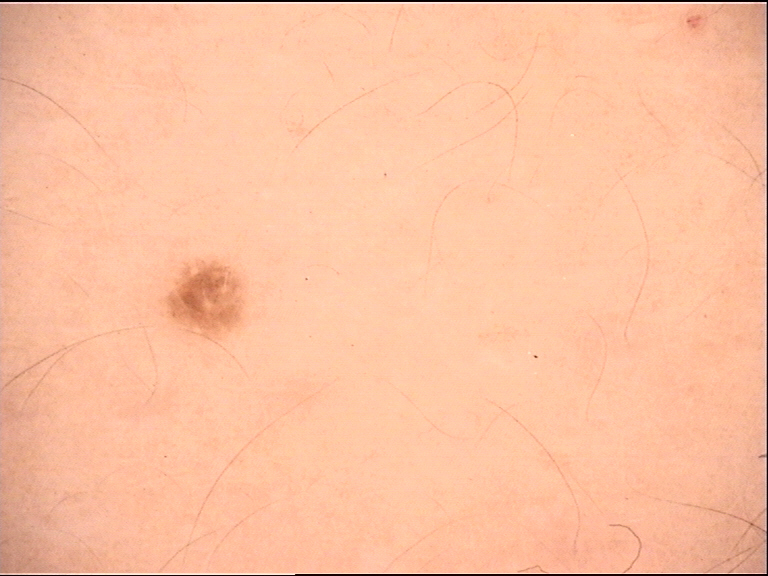The diagnosis was a dysplastic junctional nevus.